Located on the leg · no relevant lesion symptoms reported · the patient is a female aged 40–49 · the lesion is described as rough or flaky · reported duration is about one day · a close-up photograph · the contributor reports associated shortness of breath, fatigue and joint pain:
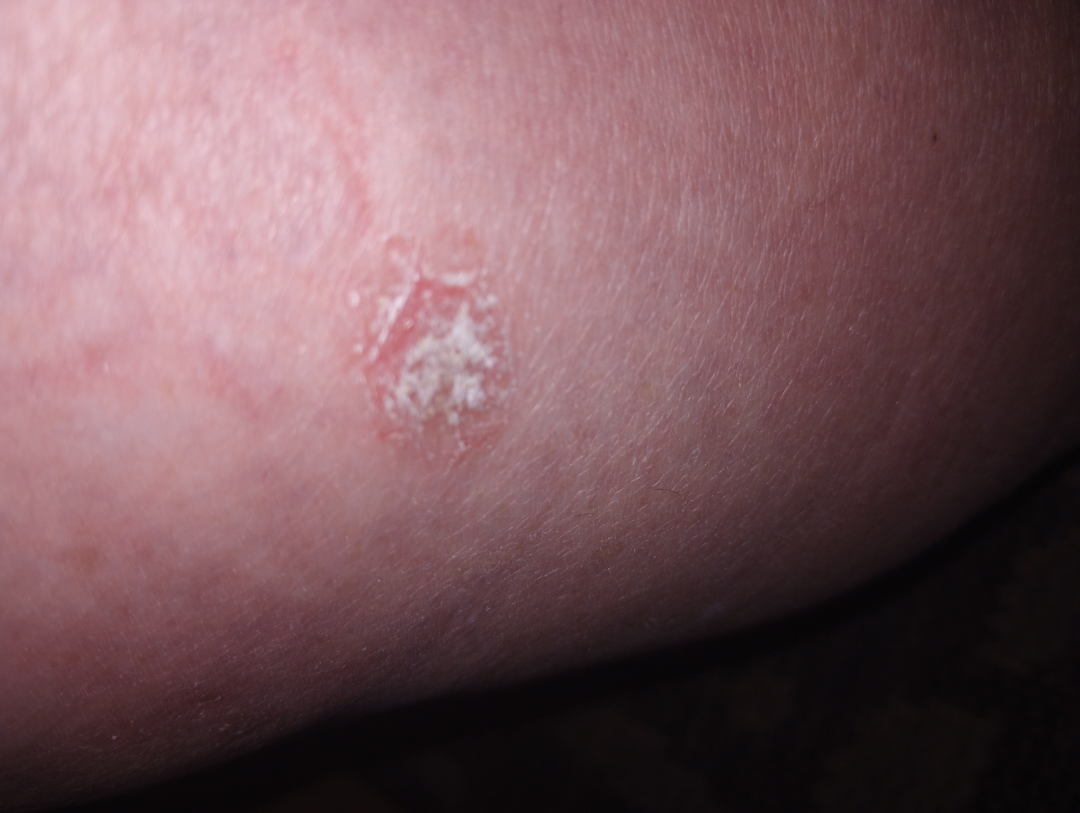Impression:
On photographic review by a dermatologist, most likely SCC/SCCIS; an alternative is SK/ISK.